Dermoscopy of a skin lesion; the patient is a male aged 43-47:
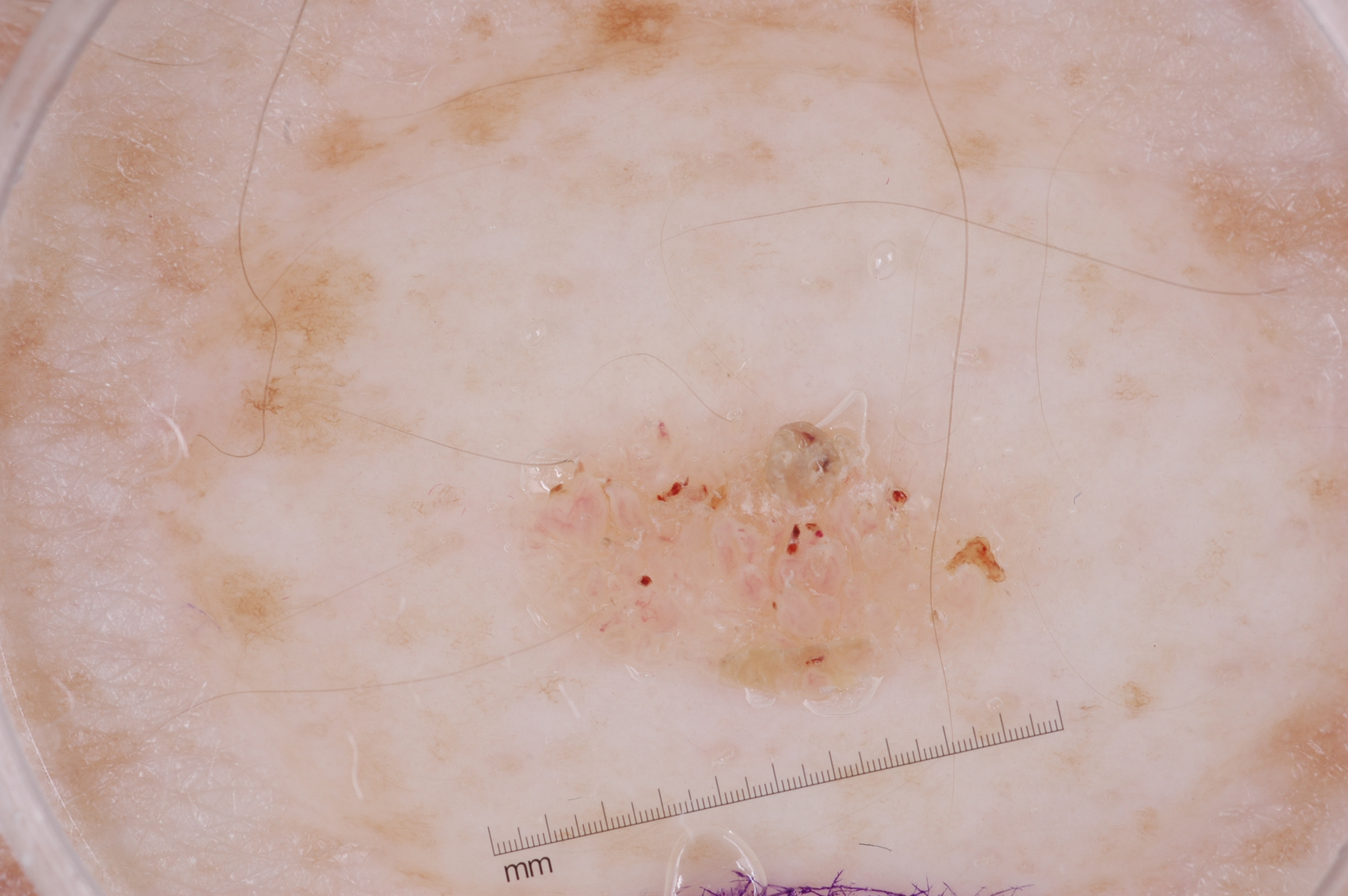The lesion occupies roughly 7% of the field. With coordinates (x1, y1, x2, y2), the lesion occupies the region 526 401 1009 701. Dermoscopy demonstrates no streaks, pigment network, milia-like cysts, or negative network. Expert review diagnosed this as a seborrheic keratosis.